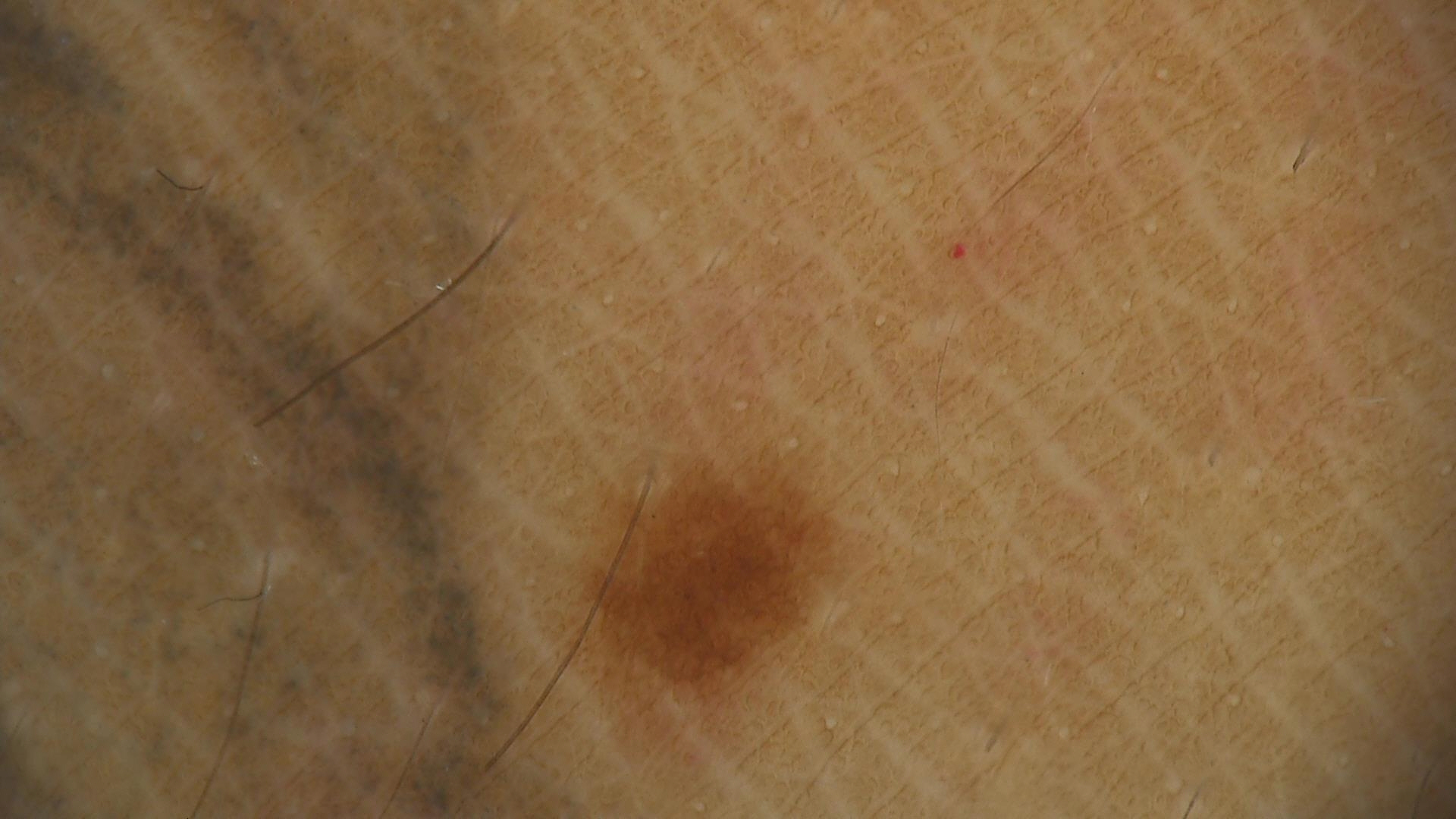{
  "image": "dermoscopy",
  "lesion_type": {
    "main_class": "banal",
    "pattern": "junctional"
  },
  "diagnosis": {
    "name": "junctional nevus",
    "code": "jb",
    "malignancy": "benign",
    "super_class": "melanocytic",
    "confirmation": "expert consensus"
  }
}